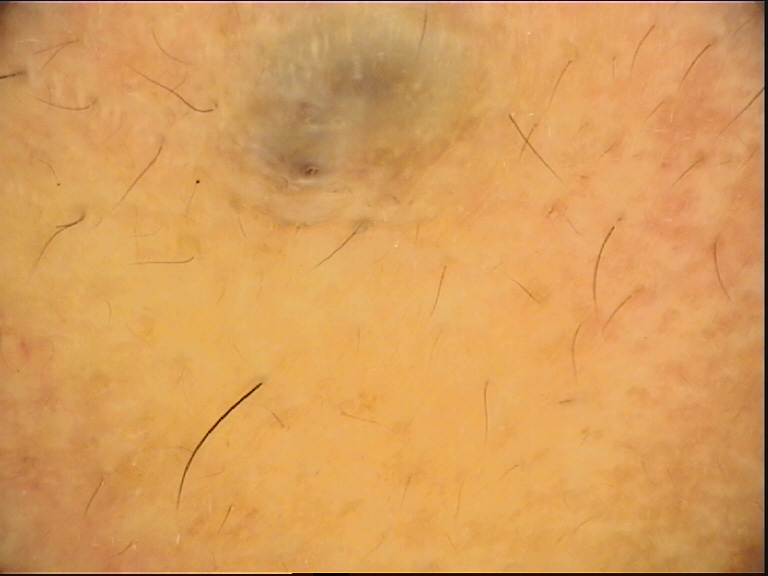A dermoscopic photograph of a skin lesion. The diagnostic label was a blue nevus.